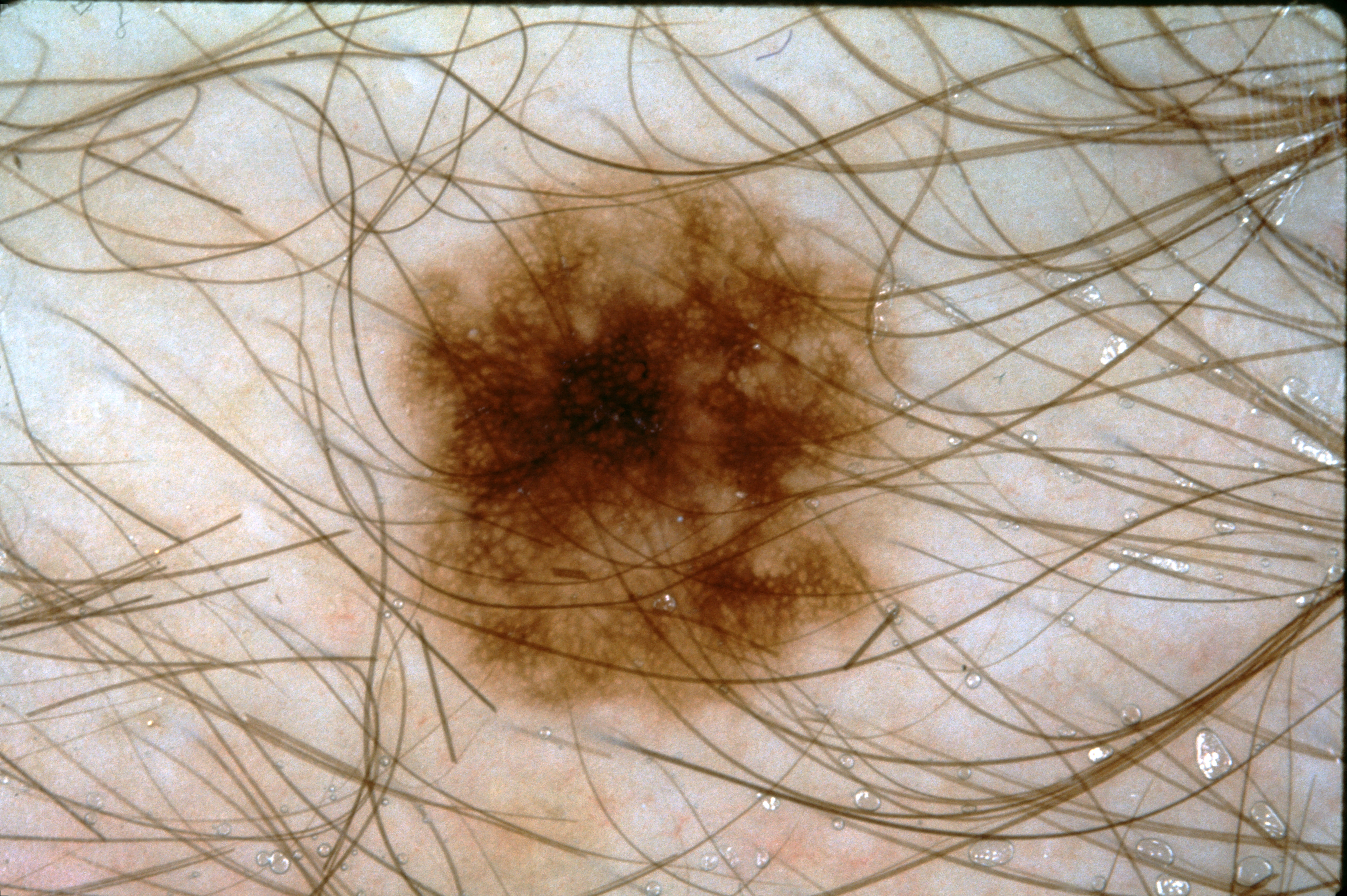A dermoscopic image of a skin lesion.
The visible lesion spans left=378, top=141, right=929, bottom=725.
The lesion takes up a moderate portion of the field.
Dermoscopically, the lesion shows pigment network.
The clinical diagnosis was a melanocytic nevus, a benign skin lesion.